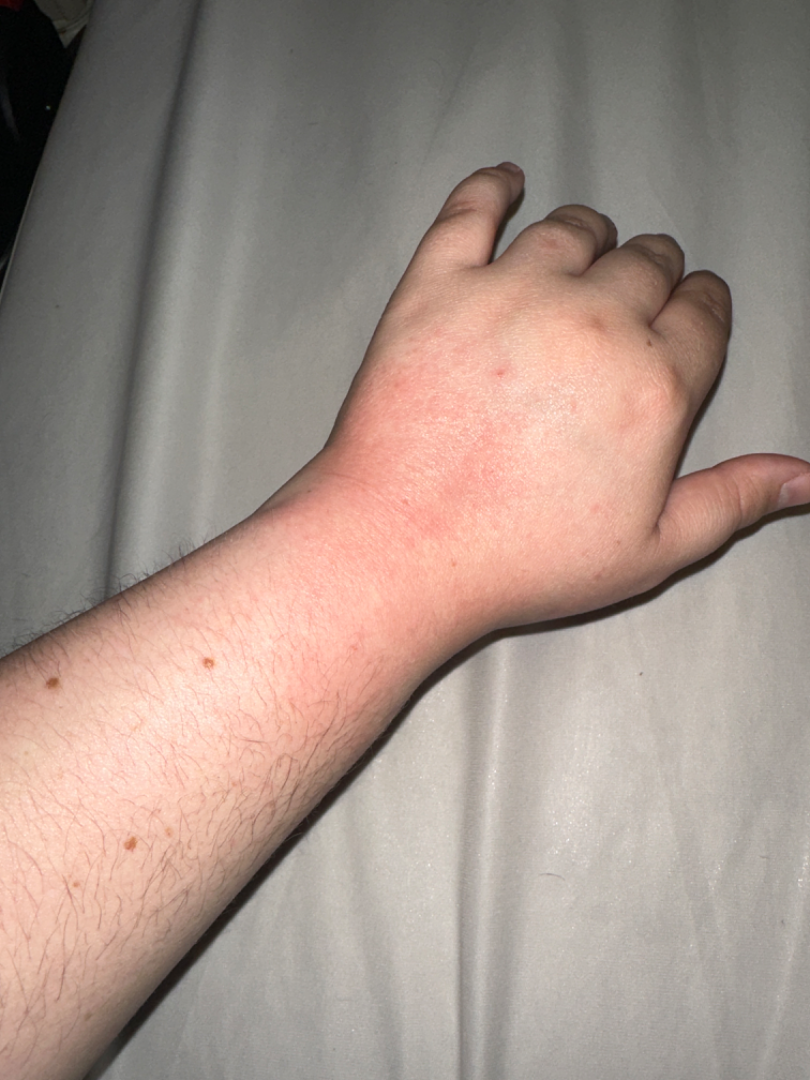The skin findings could not be characterized from the image. The lesion is described as raised or bumpy. The lesion is associated with itching. Located on the back of the hand. The condition has been present for about one day. The photo was captured at a distance.